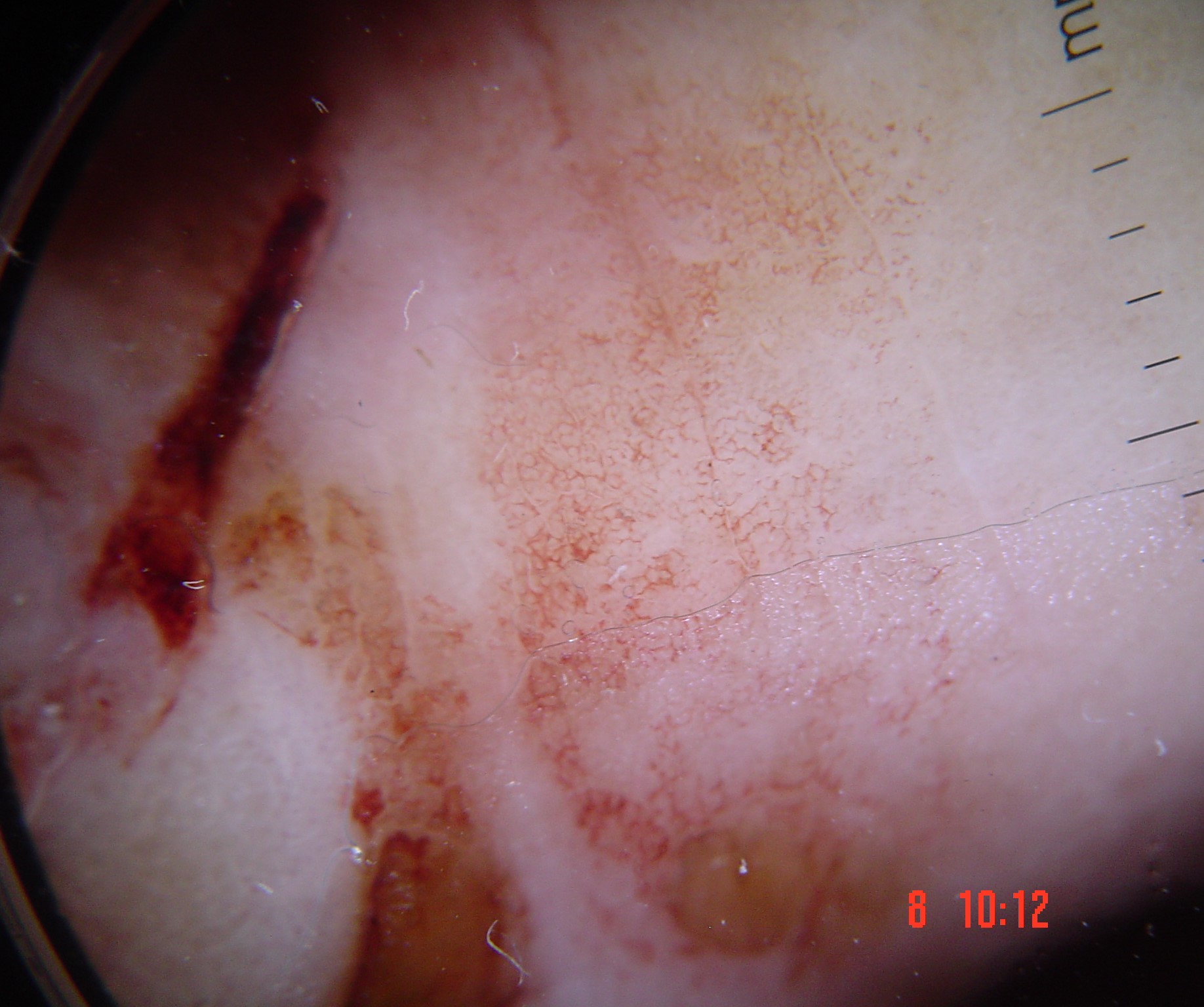<case>
<diagnosis>
<name>acral nodular melanoma</name>
<code>anm</code>
<malignancy>malignant</malignancy>
<super_class>melanocytic</super_class>
<confirmation>histopathology</confirmation>
</diagnosis>
</case>